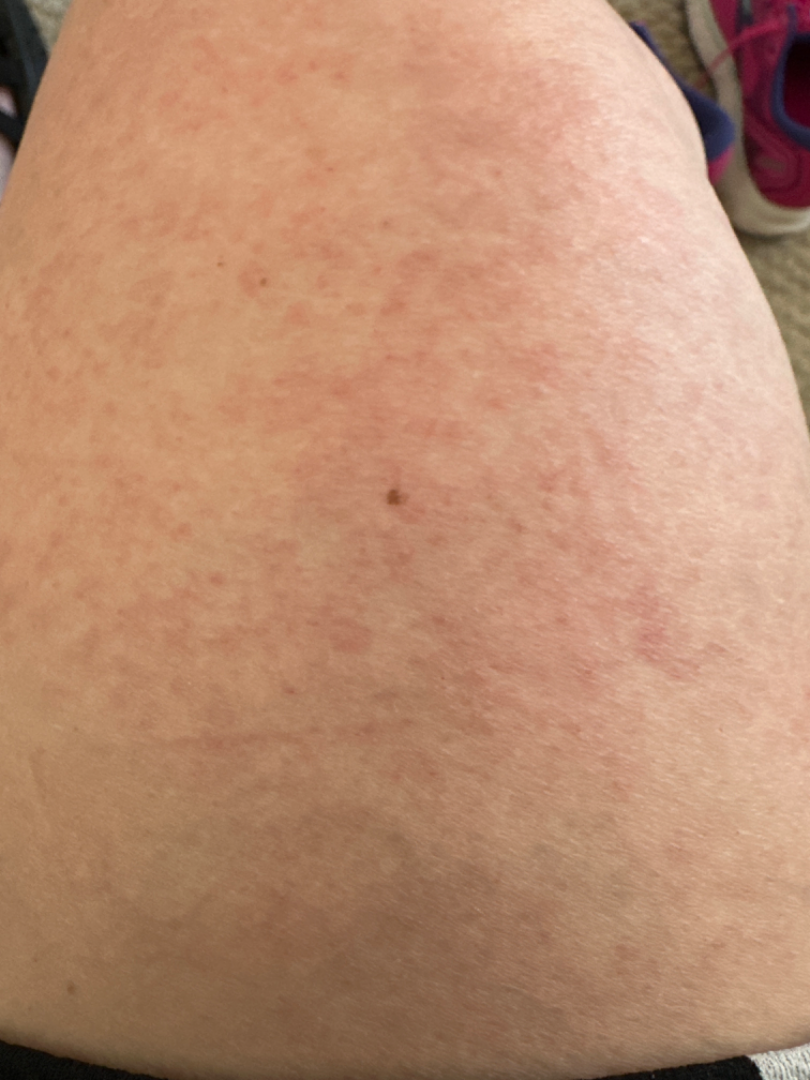associated systemic symptoms — none reported | described texture — raised or bumpy | photo taken — close-up | patient-reported symptoms — itching and bothersome appearance | subject — female, age 40–49 | skin tone — Fitzpatrick skin type II; non-clinician graders estimated Monk skin tone scale 2 or 3 (two reviewer pools) | patient describes the issue as — a rash | site — leg | present for — about one day | assessment — the leading impression is Keratosis pilaris; also consider Folliculitis; with consideration of Eczema.